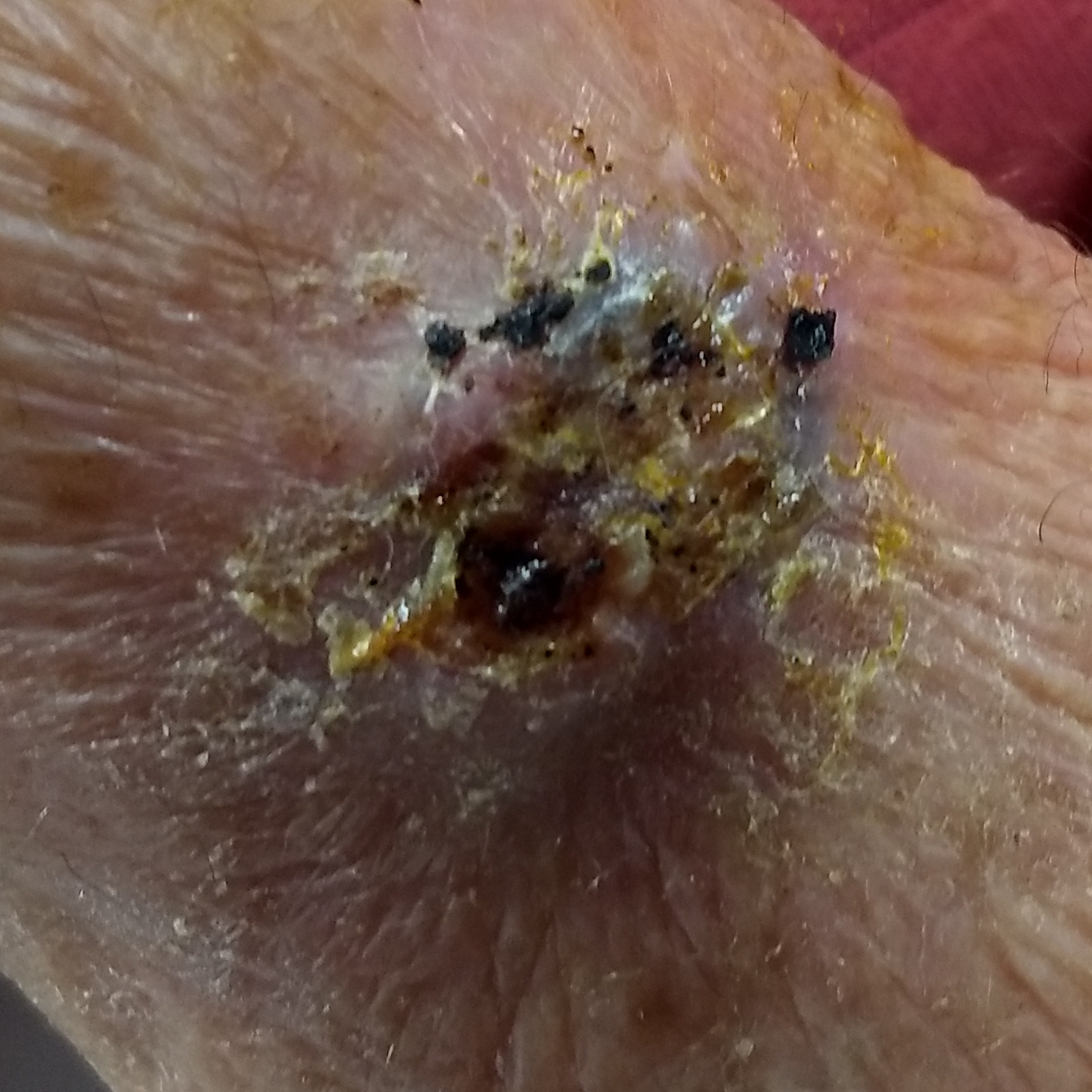image type: clinical photograph
subject: male, 83 years of age
skin phototype: II
risk factors: tobacco use
lesion size: 30x20 mm
patient-reported symptoms: pain, elevation, itching, bleeding
diagnostic label: basal cell carcinoma (biopsy-proven)